A female subject aged around 70; a dermoscopic view of a skin lesion:
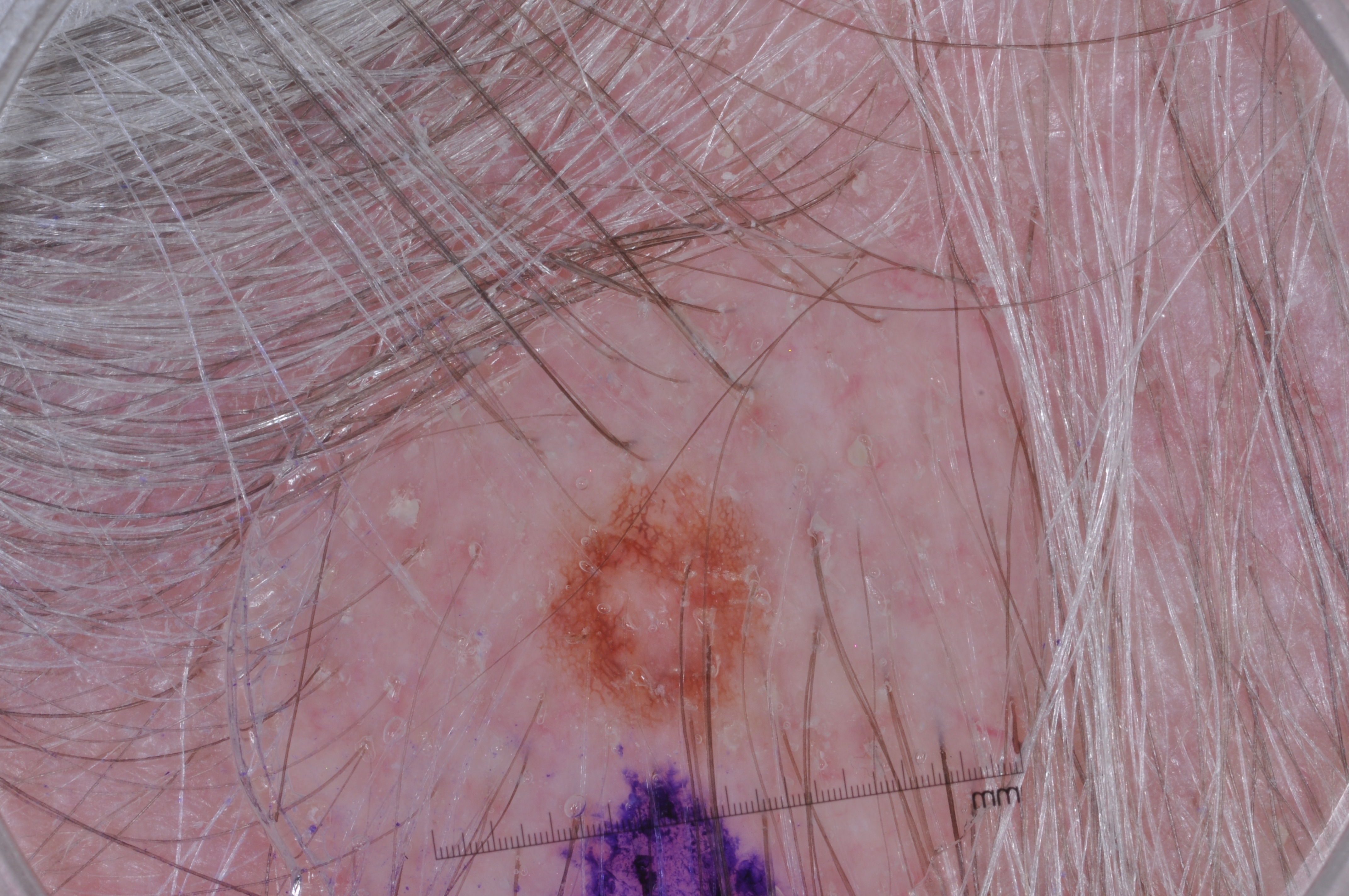Q: What does dermoscopy show?
A: pigment network; absent: negative network, milia-like cysts, and streaks
Q: What is the lesion's bounding box?
A: bbox(531, 466, 783, 740)
Q: What is the diagnosis?
A: a melanocytic nevus